A dermoscopic image of a skin lesion.
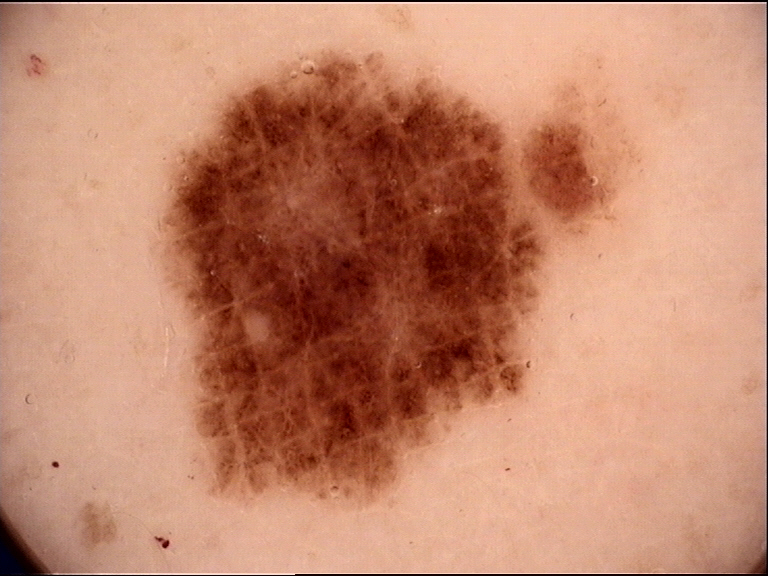Conclusion: The diagnostic label was a benign lesion — a dysplastic junctional nevus.